The photograph is a close-up of the affected area. The arm is involved. Female contributor, age 18–29: 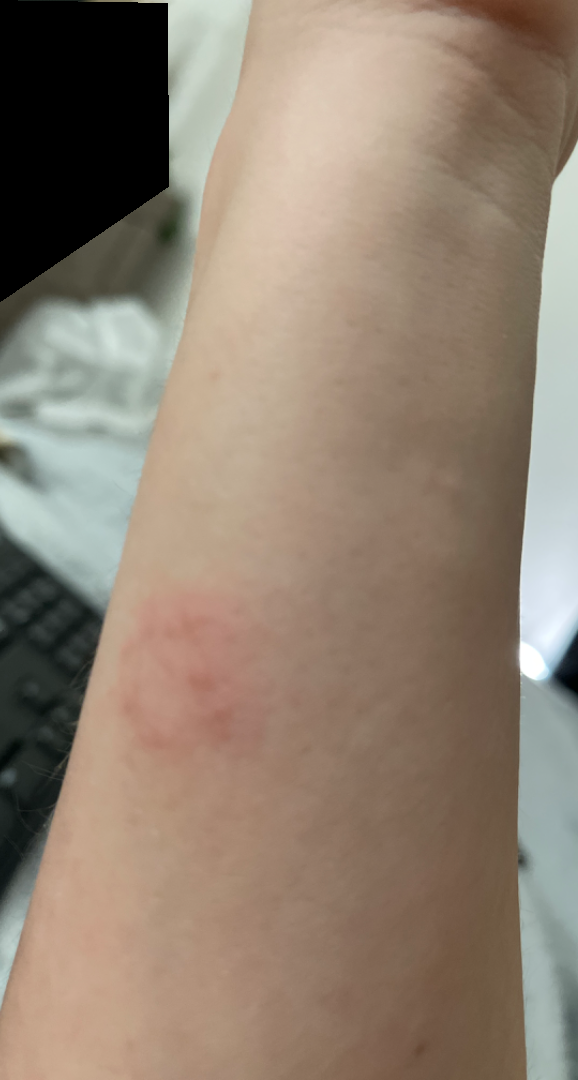assessment=no discernible pathology